The lesion involves the arm, close-up view, the contributor is a male aged 18–29:
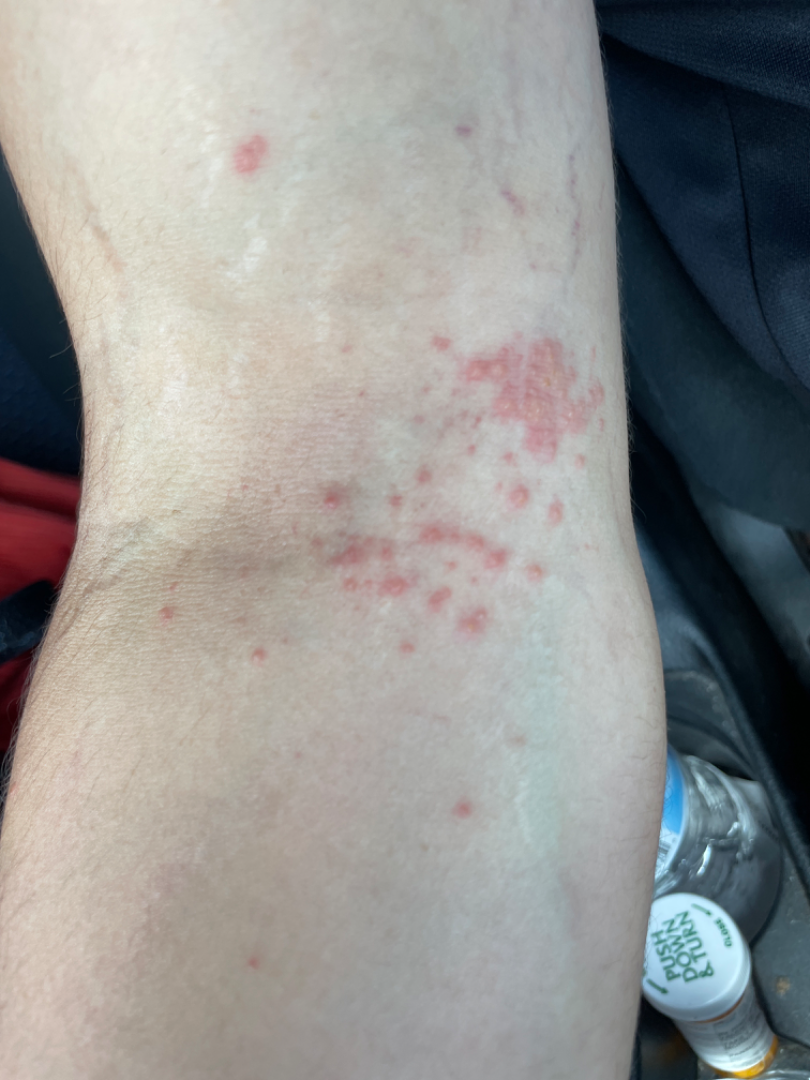In keeping with Allergic Contact Dermatitis.